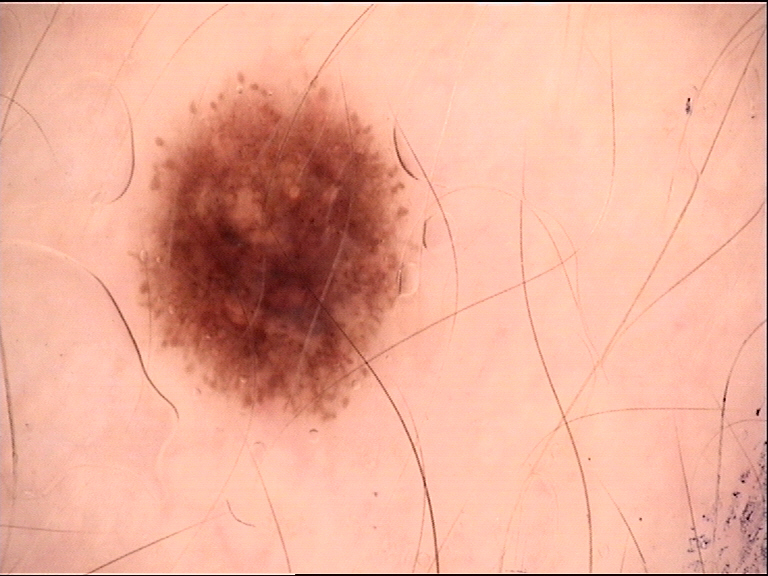A dermoscopy image of a single skin lesion. The diagnosis was a benign lesion — a dysplastic junctional nevus.